The contributor is a male aged 40–49; close-up view; the affected area is the back of the hand, arm, front of the torso and top or side of the foot: 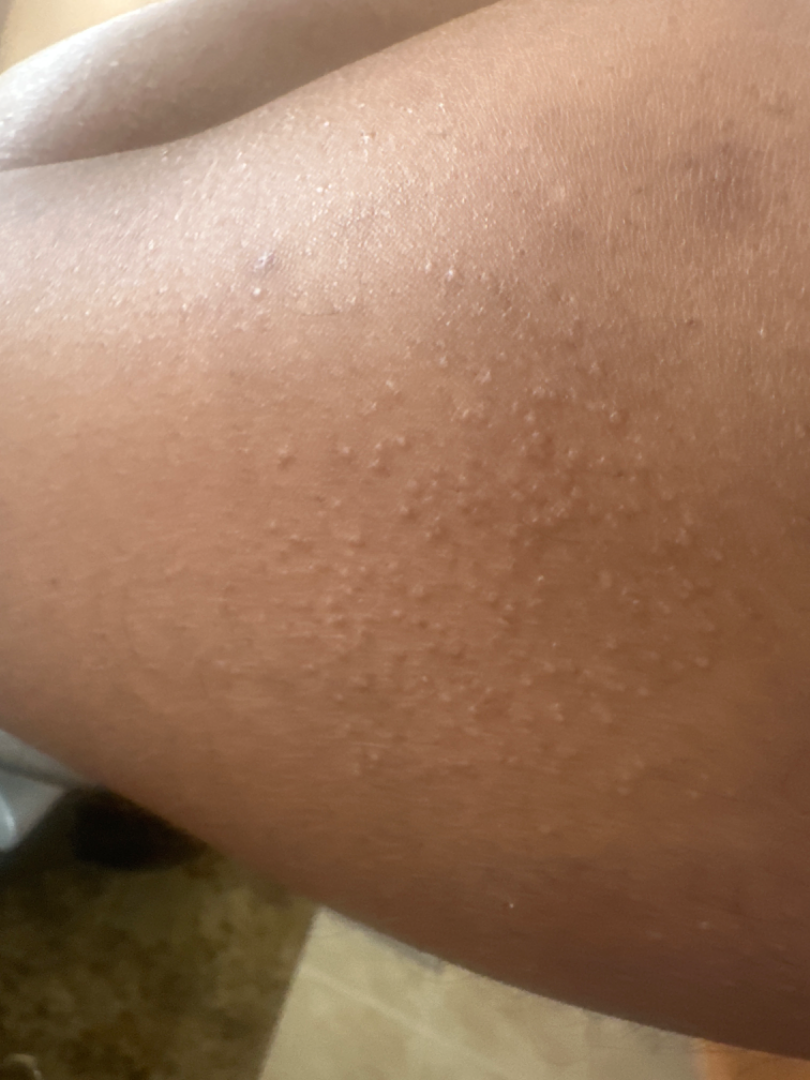On remote dermatologist review, Eczema (0.50); Chronic dermatitis, NOS (0.50).